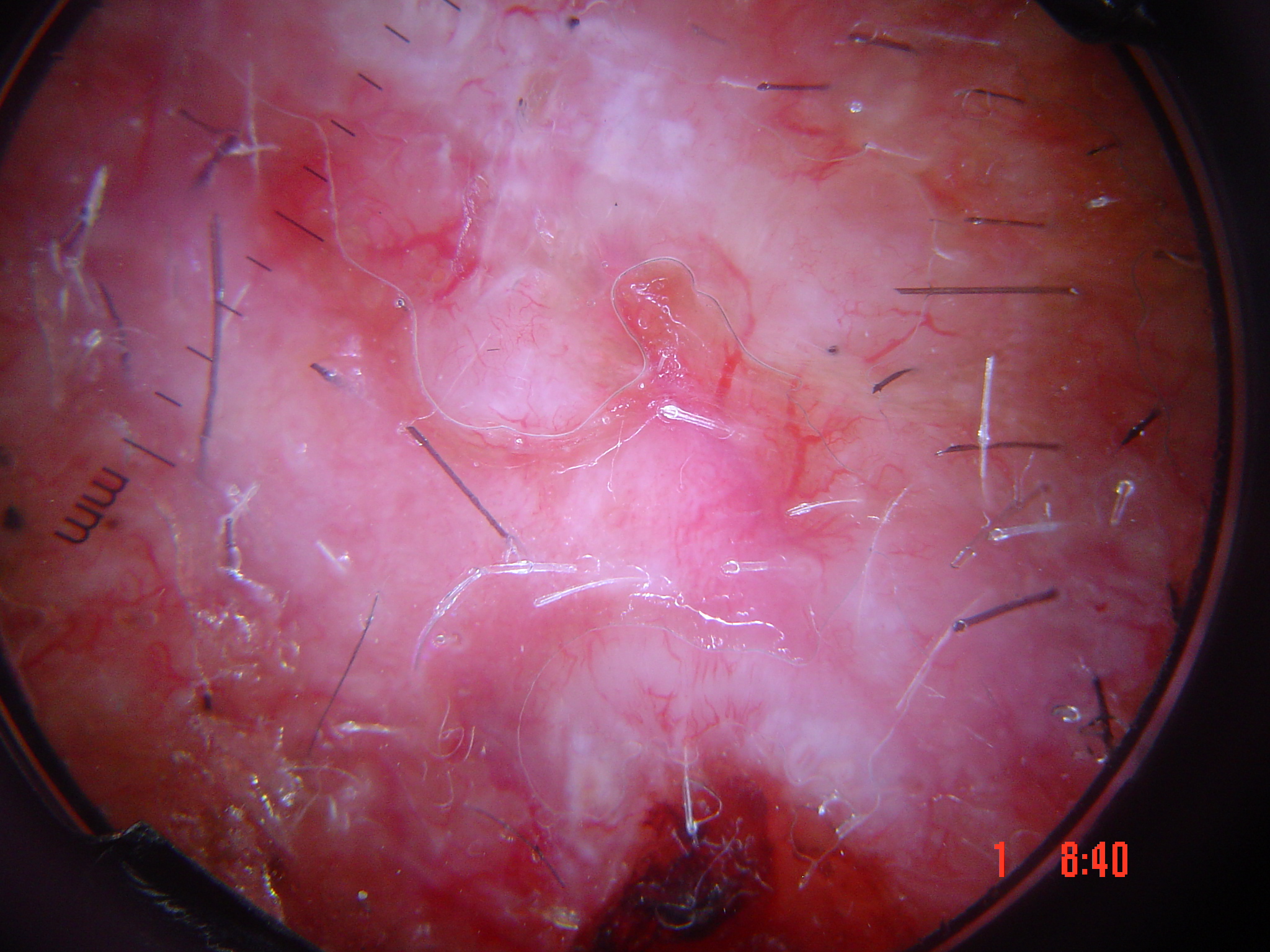Confirmed on histopathology as a keratinocytic lesion — a basal cell carcinoma.